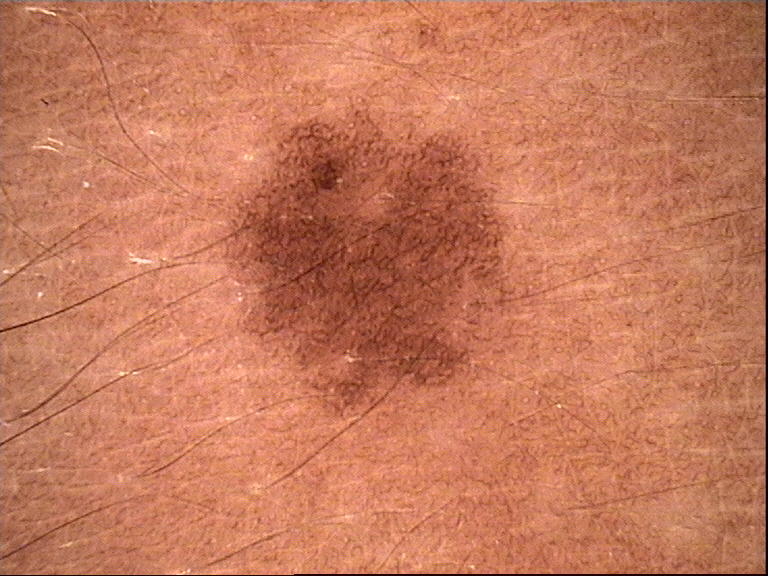| key | value |
|---|---|
| modality | dermatoscopy |
| diagnosis | dysplastic junctional nevus (expert consensus) |